Dermoscopy of a skin lesion.
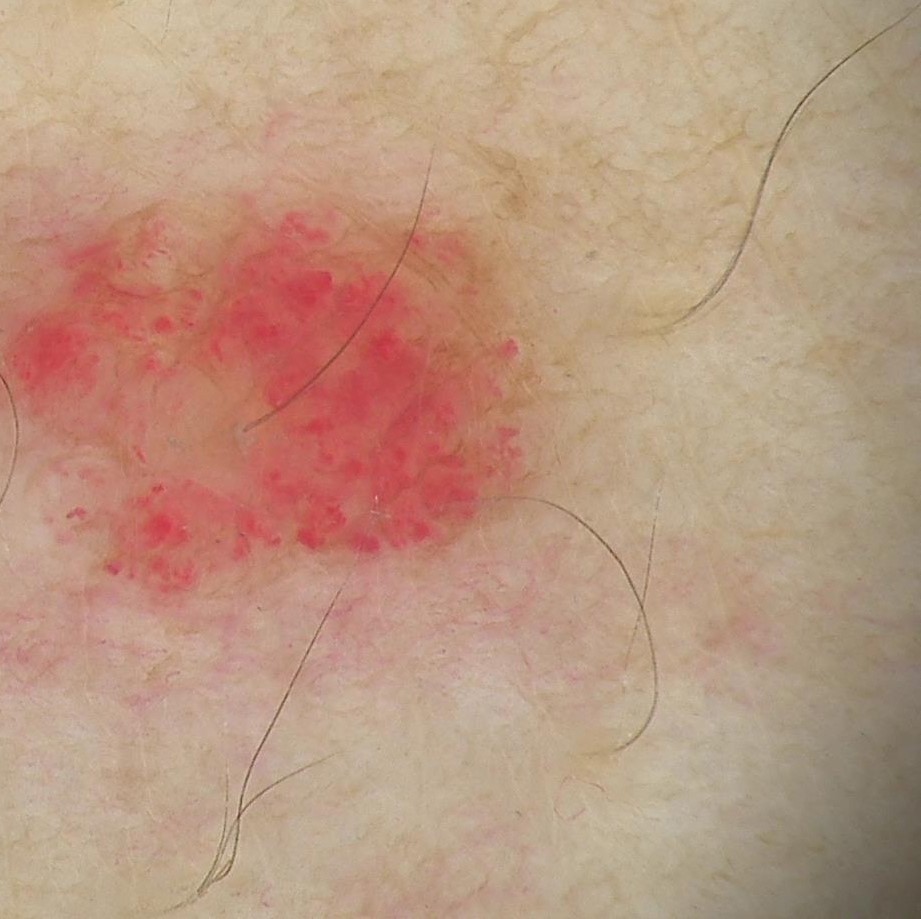Labeled as a hemangioma.